Numerous moles by the patient's own estimate; the patient says their skin reddens with sun exposure; a skin lesion imaged with a dermatoscope.
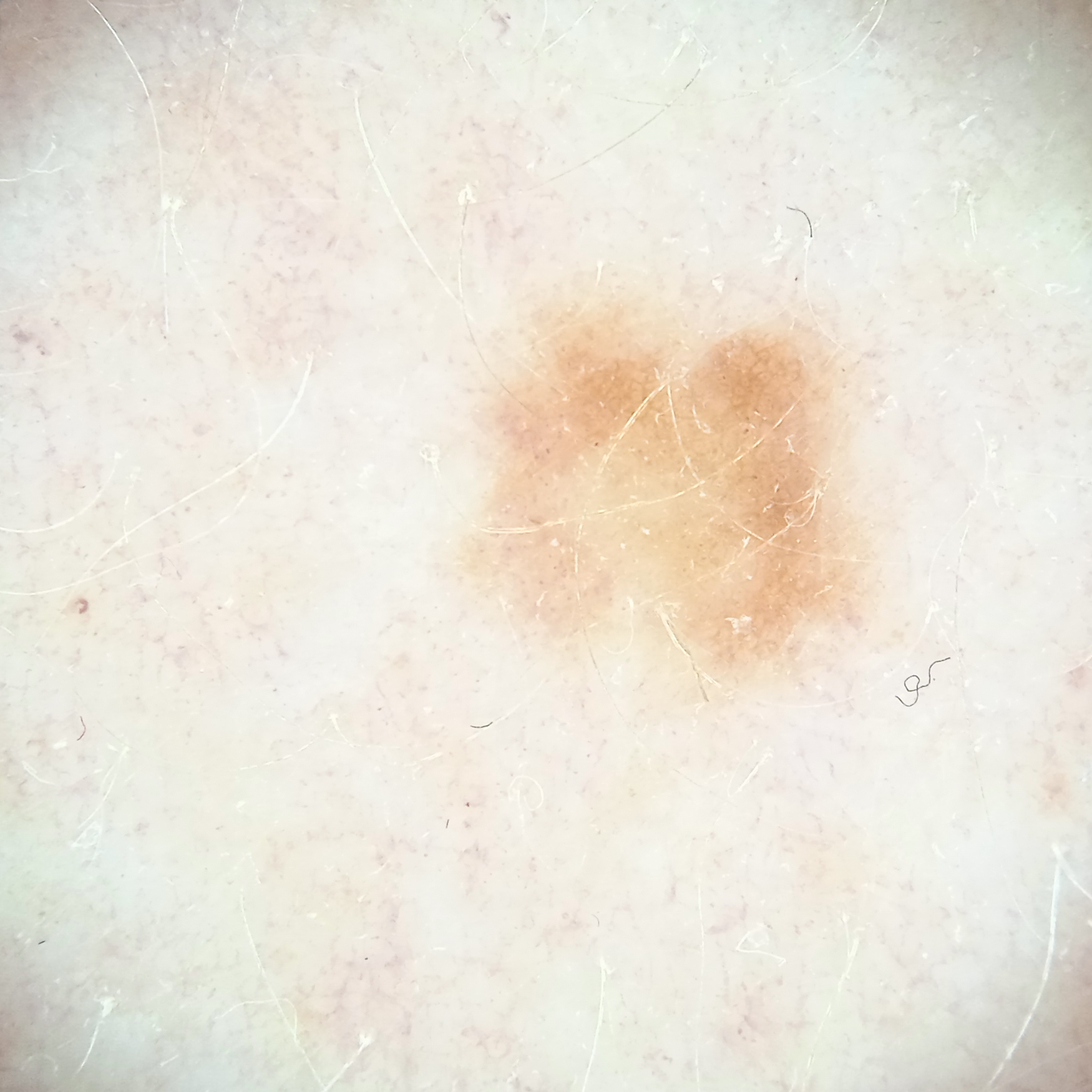The lesion involves an arm. The lesion is about 4.7 mm across. Dermatologist review favored an atypical (dysplastic) nevus.